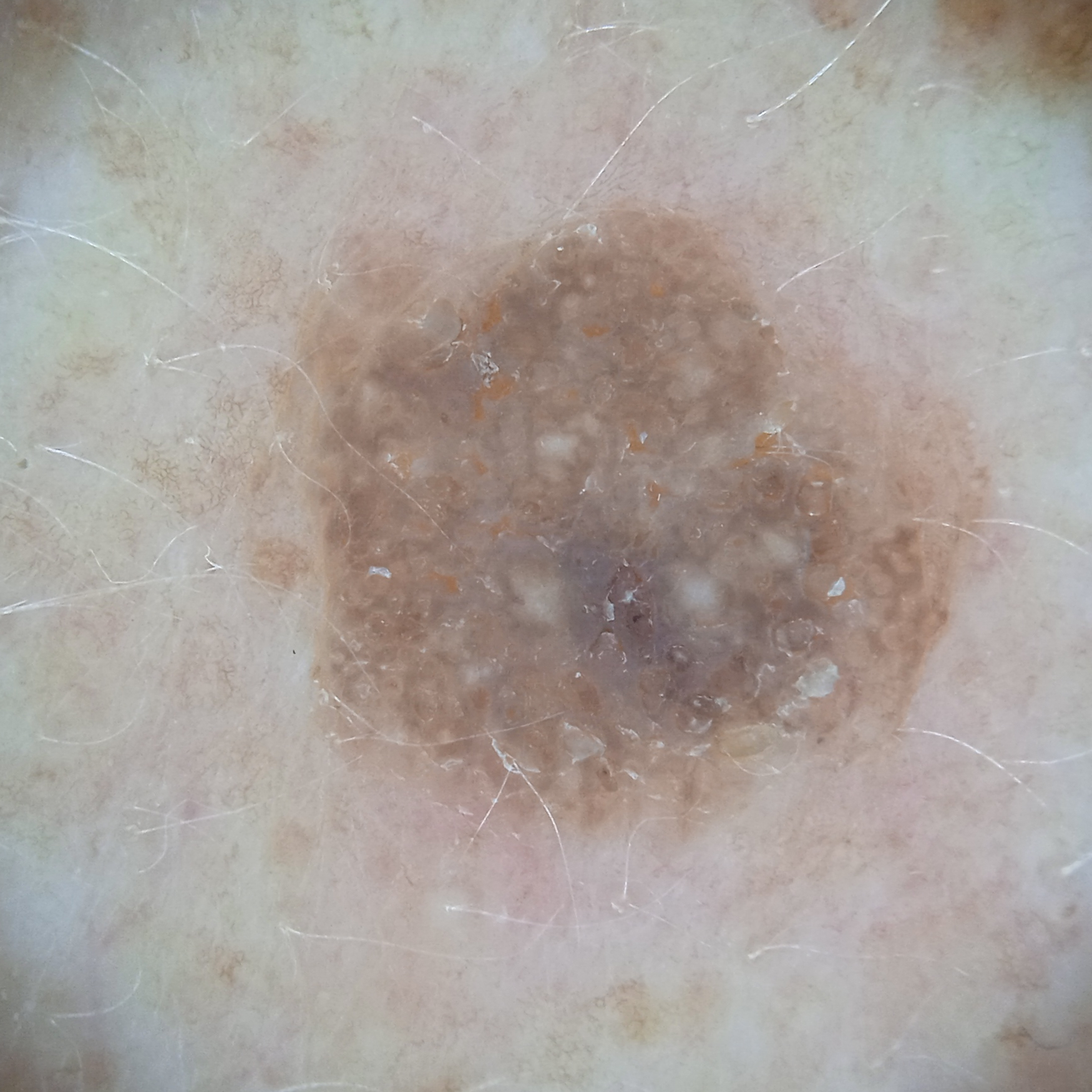| field | value |
|---|---|
| sun reaction | skin tans without first burning |
| clinical context | research study (no referral diagnosis) |
| patient | female, aged 78 |
| nevus count | numerous melanocytic nevi |
| imaging | dermoscopic image |
| body site | the back |
| size | 7.3 mm |
| assessment | seborrheic keratosis (dermatologist consensus) |